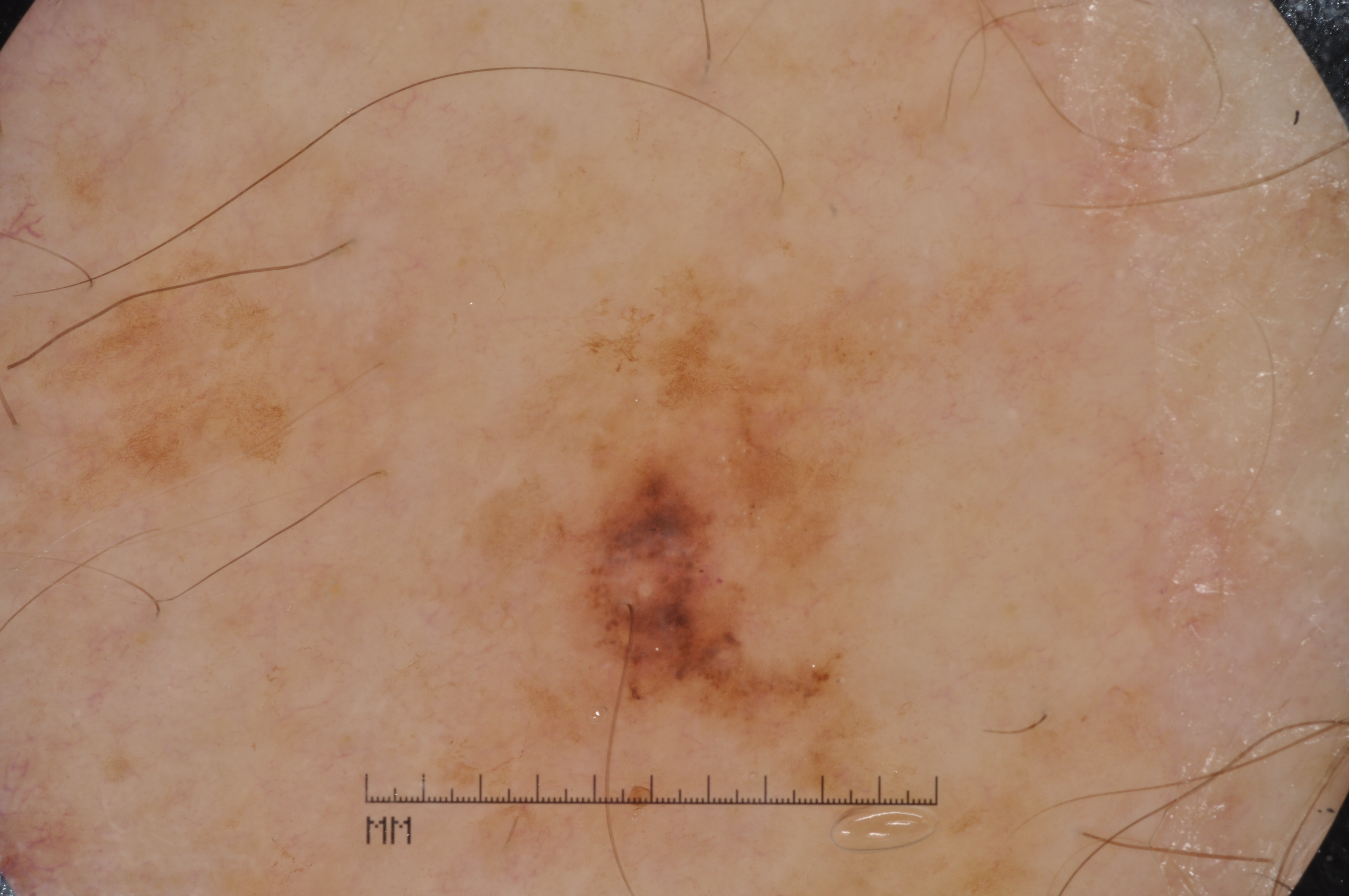A dermoscopy image of a single skin lesion.
The dermoscopic pattern shows pigment network and milia-like cysts.
The lesion covers approximately 13% of the dermoscopic field.
Lesion location: left=513, top=261, right=924, bottom=798.
On biopsy, the diagnosis was a melanoma.